Texture is reported as raised or bumpy. The contributor is 50–59, male. The patient also reports fatigue. The lesion involves the back of the hand, palm, head or neck, leg and arm. The patient reports enlargement, itching and bothersome appearance. This image was taken at a distance. The patient reports the condition has been present for one to four weeks. Self-categorized by the patient as skin that appeared healthy to them: 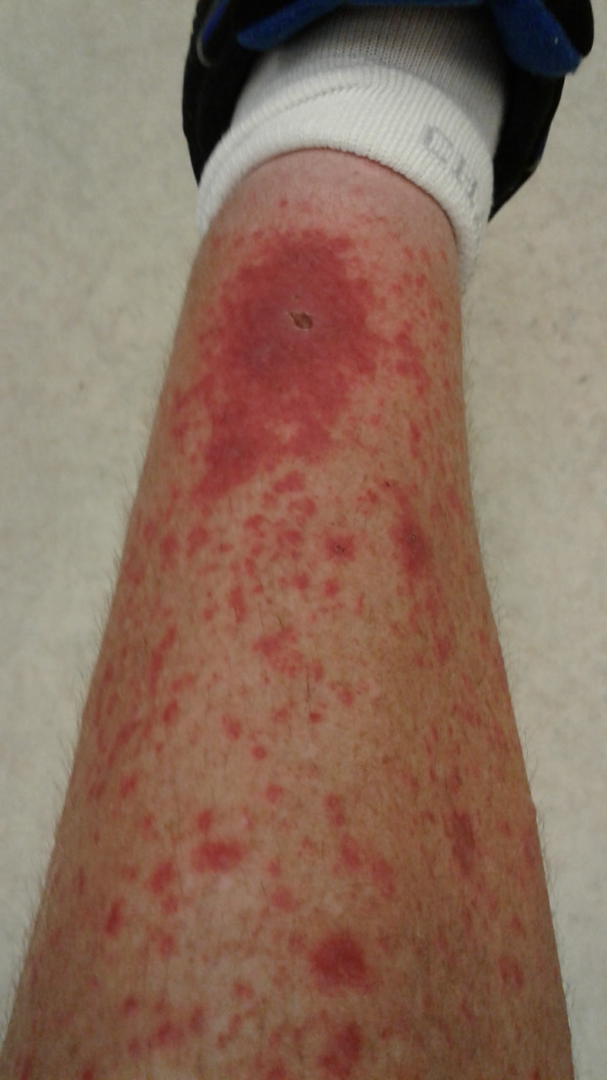Findings:
On teledermatology review: the leading impression is Leukocytoclastic Vasculitis; less probable is Psoriasis; less likely is Eczema.